A dermoscopic image of a skin lesion: 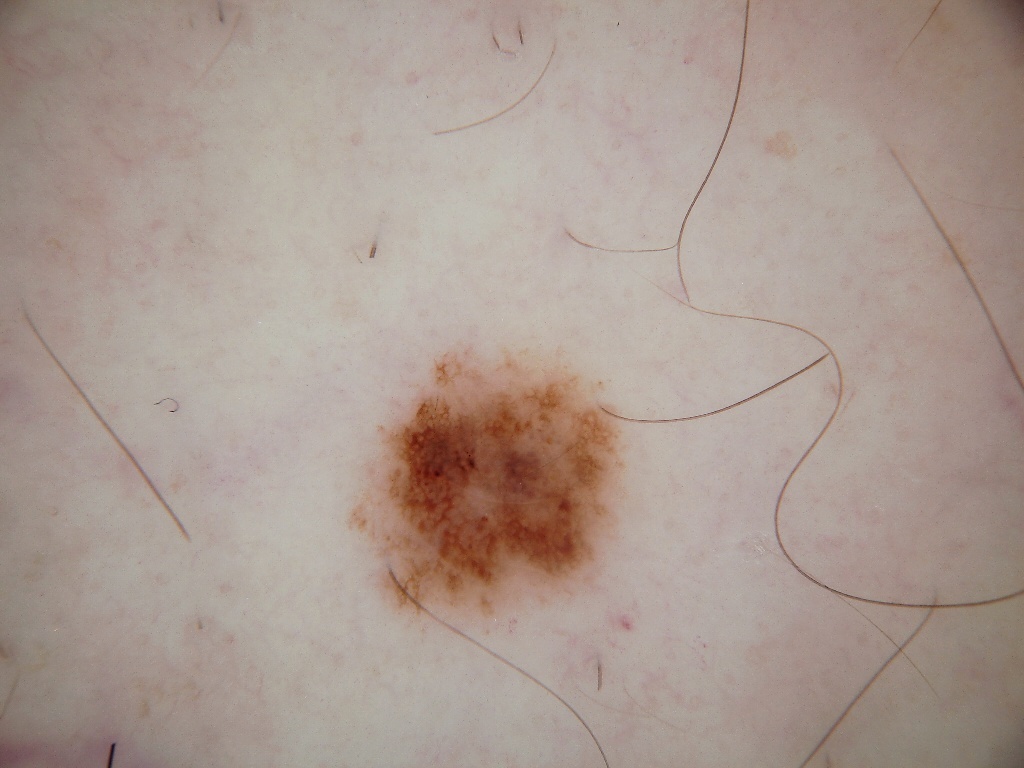| key | value |
|---|---|
| dermoscopic findings | pigment network; absent: globules, streaks, milia-like cysts, and negative network |
| bounding box | 350 354 622 620 |
| impression | a melanocytic nevus, a benign skin lesion |